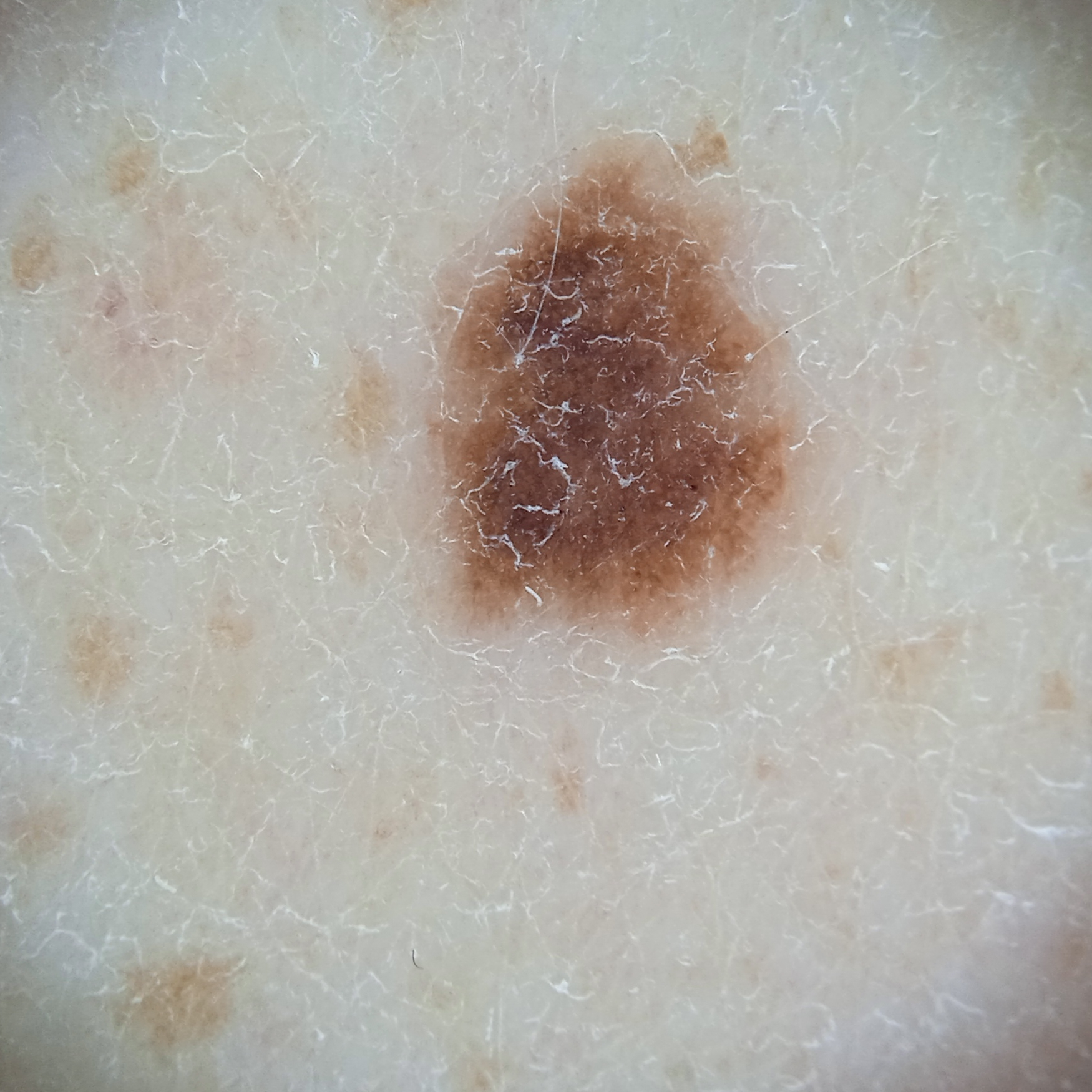| field | value |
|---|---|
| image | dermoscopy |
| referral | research study (no referral diagnosis) |
| nevus count | few melanocytic nevi overall |
| risk factors | a personal history of cancer |
| body site | the back |
| diameter | 5.6 mm |
| assessment | melanocytic nevus (dermatologist consensus) |